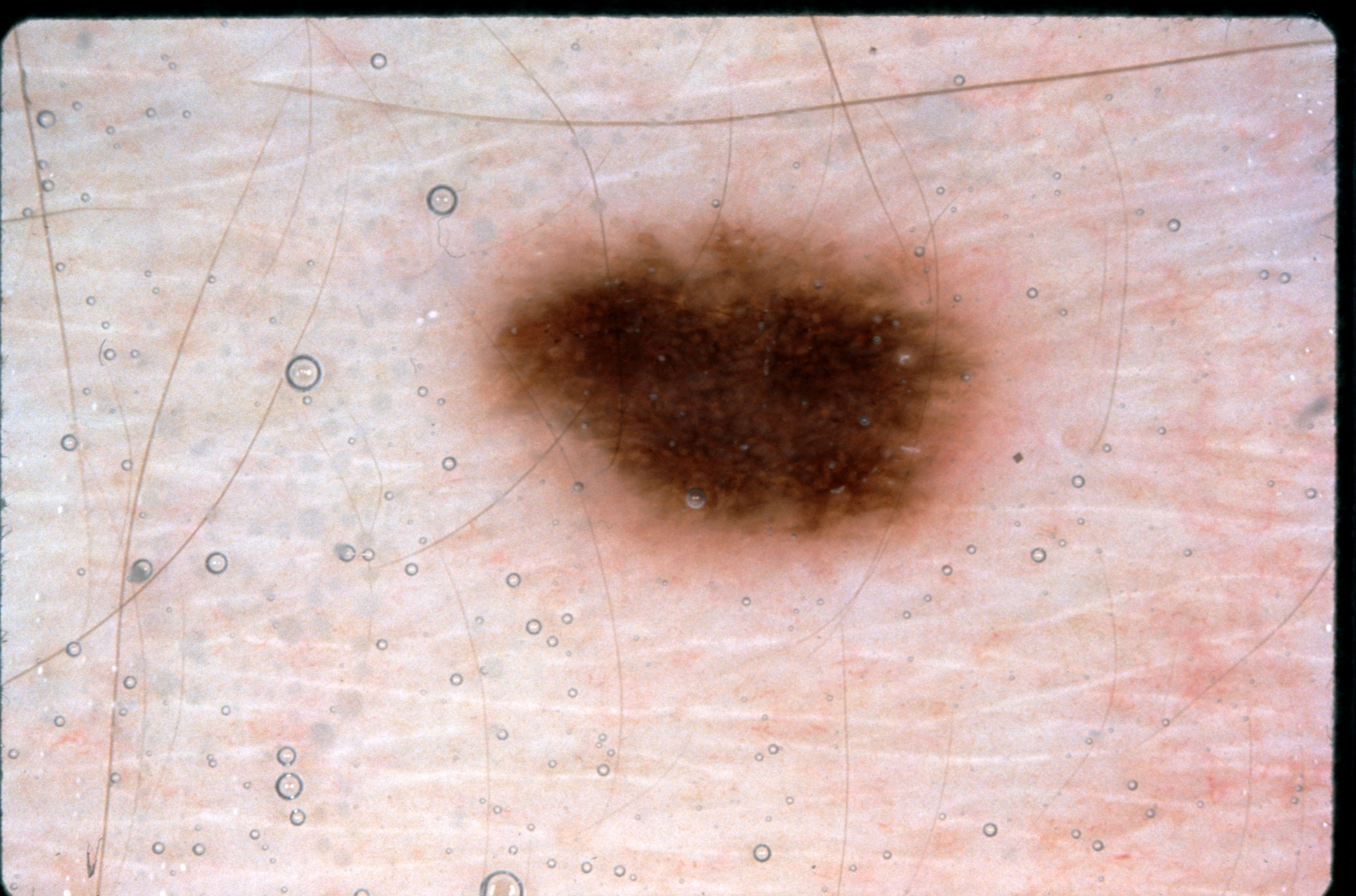Case summary: A dermoscopy image of a single skin lesion. The subject is a male approximately 35 years of age. The lesion is bounded by [462, 181, 1023, 575]. Dermoscopically, the lesion shows pigment network; no negative network, streaks, or milia-like cysts. Conclusion: Consistent with a melanocytic nevus.